The head or neck and leg are involved; the subject is a female aged 18–29; this image was taken at an angle:
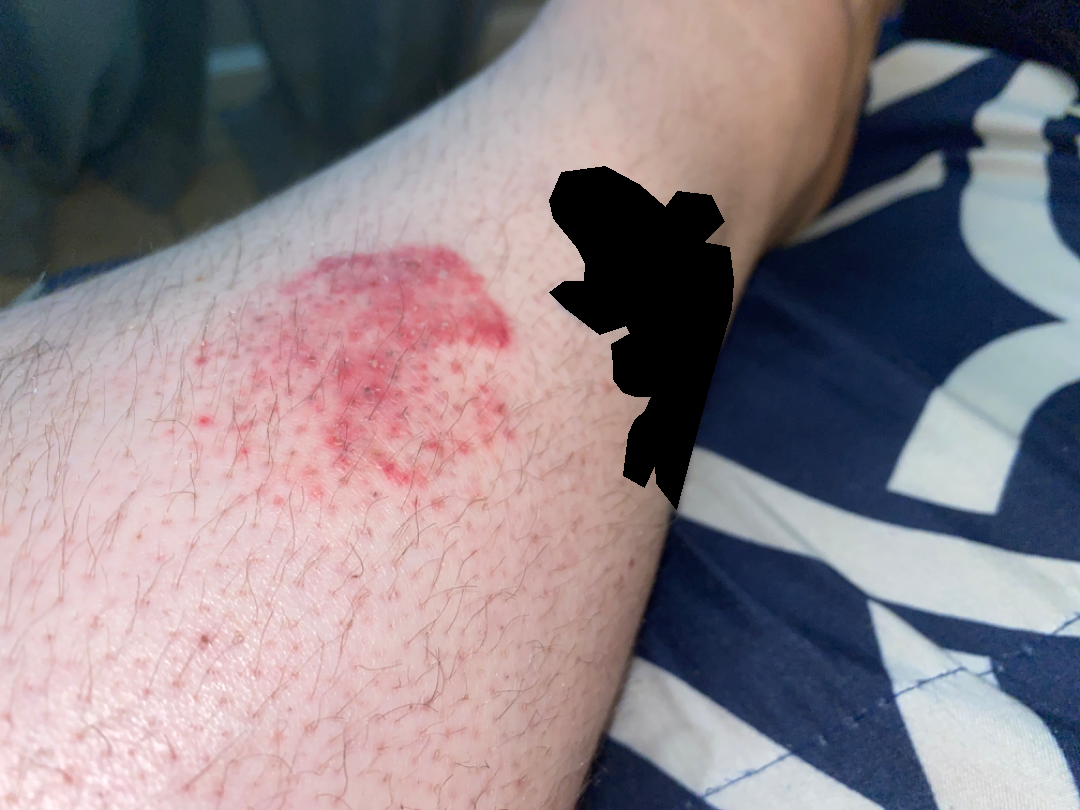Findings:
– symptoms — itching and enlargement
– constitutional symptoms — none reported
– described texture — rough or flaky and raised or bumpy
– duration — one to four weeks
– dermatologist impression — in keeping with Acute dermatitis, NOS